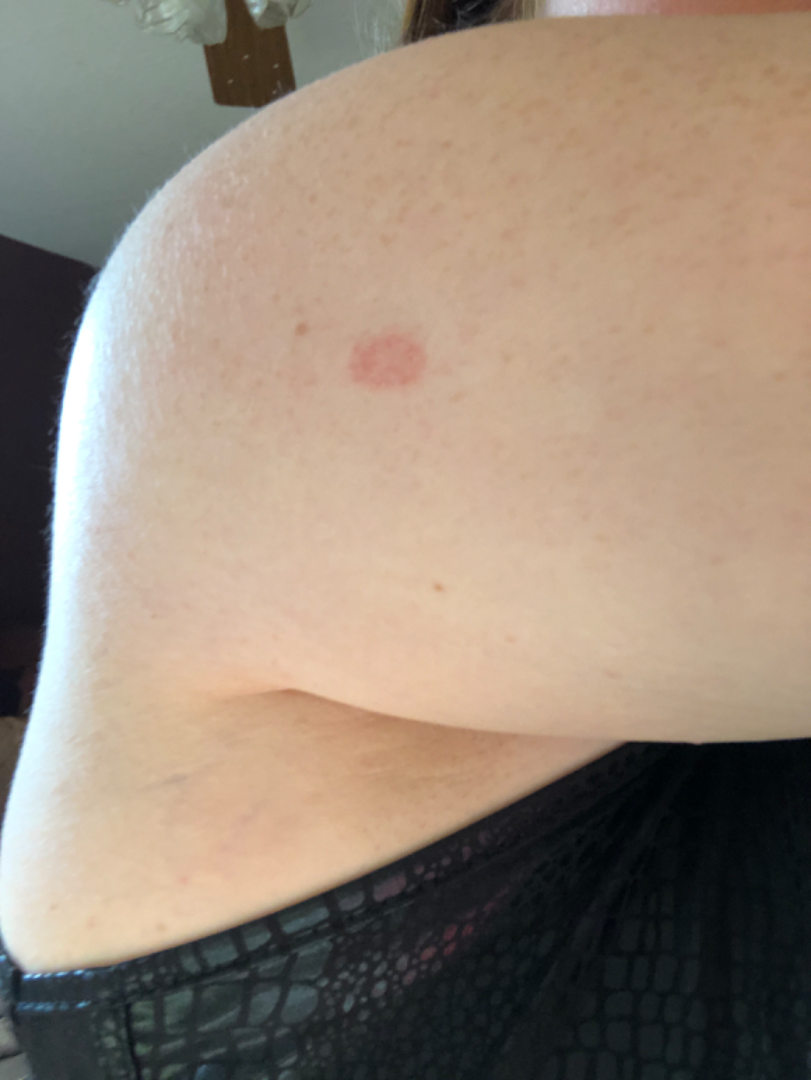No differential diagnosis could be assigned on photographic review.